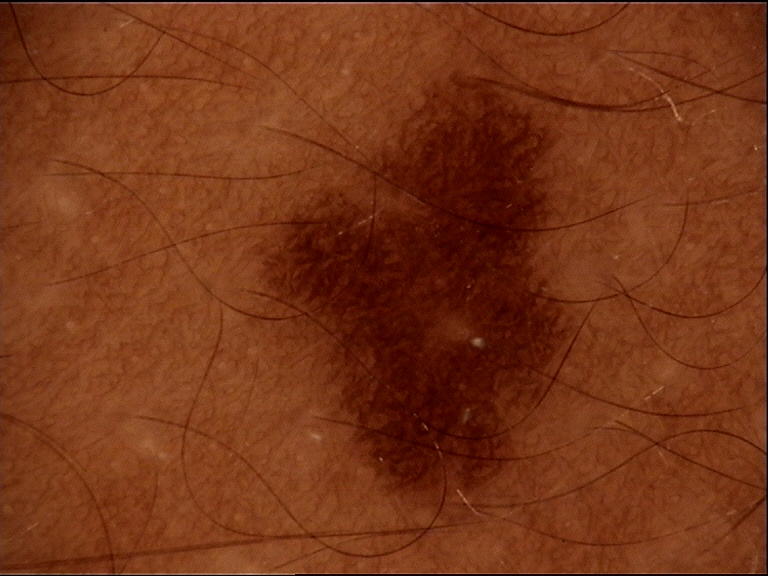{"image": "dermoscopy", "diagnosis": {"name": "dysplastic junctional nevus", "code": "jd", "malignancy": "benign", "super_class": "melanocytic", "confirmation": "expert consensus"}}